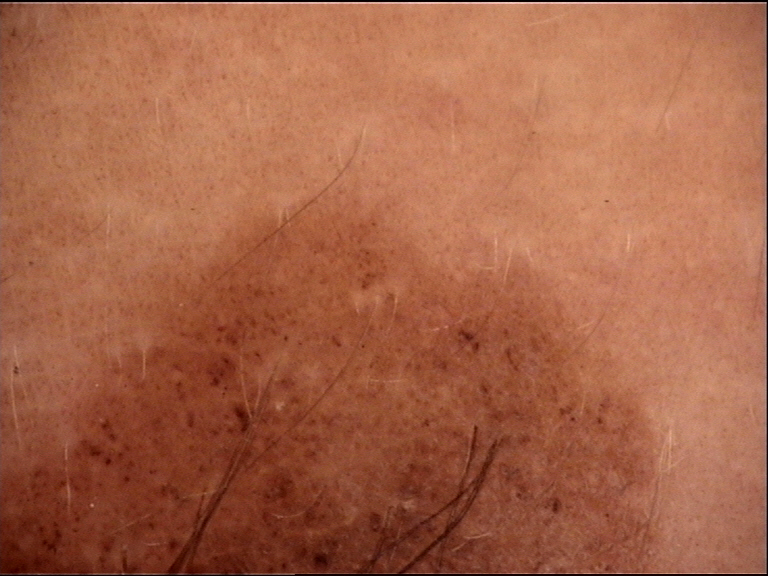image type = dermoscopy; diagnosis = congenital compound nevus (expert consensus).